A dermoscopic photograph of a skin lesion.
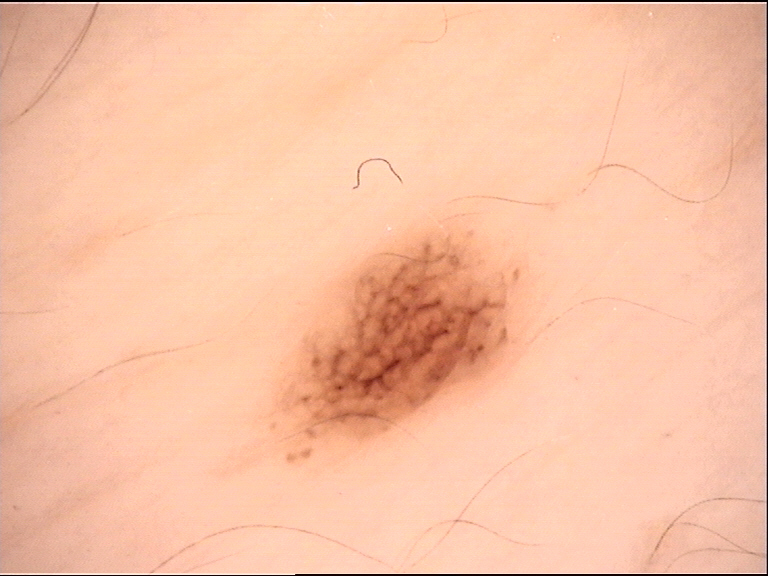Impression: Labeled as a dysplastic junctional nevus.